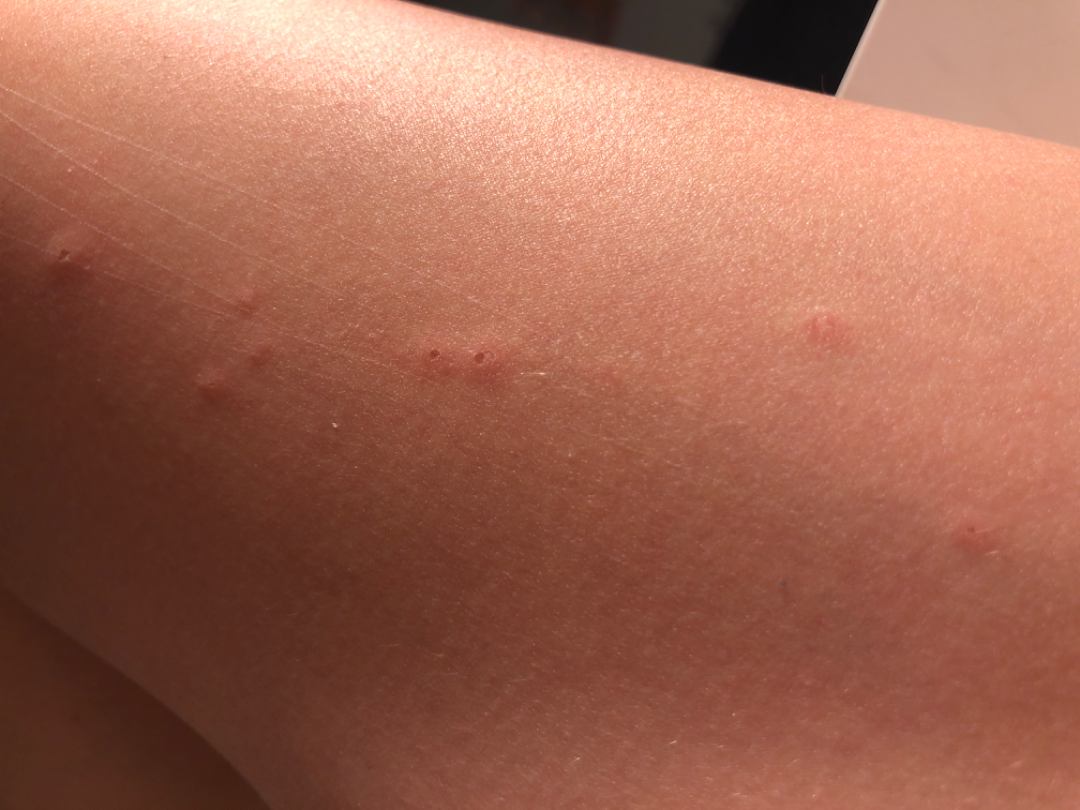History:
The subject is female. An image taken at an angle. Located on the leg.
Impression:
On remote dermatologist review: most consistent with Insect Bite; also on the differential is Molluscum Contagiosum; an alternative is Allergic Contact Dermatitis; less likely is Urticaria.